Close-up view; female subject, age 18–29 — 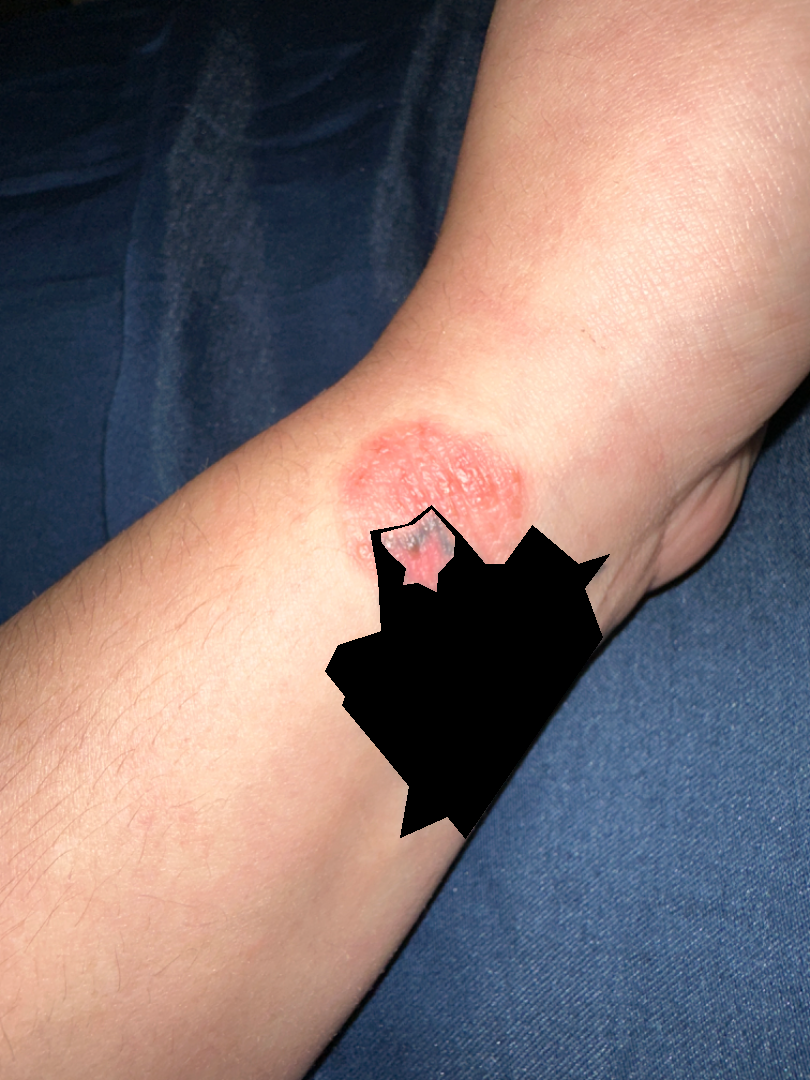clinical impression = a single dermatologist reviewed the case: the differential is split between Eczema, Psoriasis and Allergic Contact Dermatitis